This is a dermoscopic photograph of a skin lesion · a female patient, in their mid-30s.
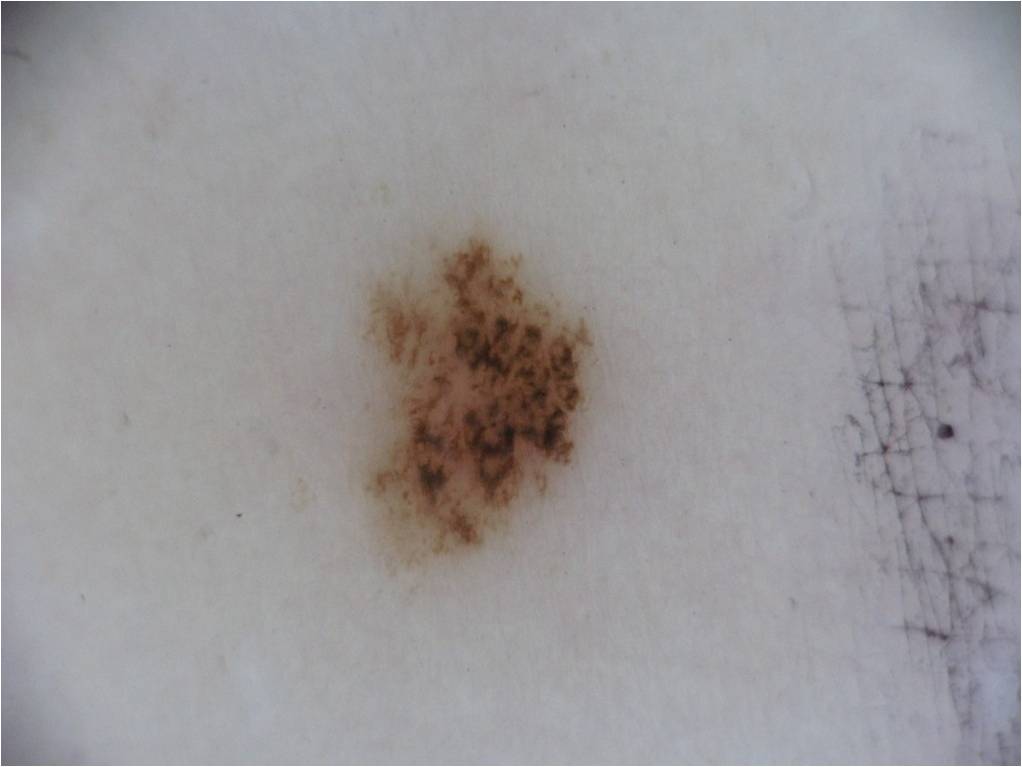With coordinates (x1, y1, x2, y2), the lesion's extent is [351, 223, 600, 567].
The dermoscopic pattern shows no globules, streaks, pigment network, negative network, or milia-like cysts.
Consistent with a melanocytic nevus.